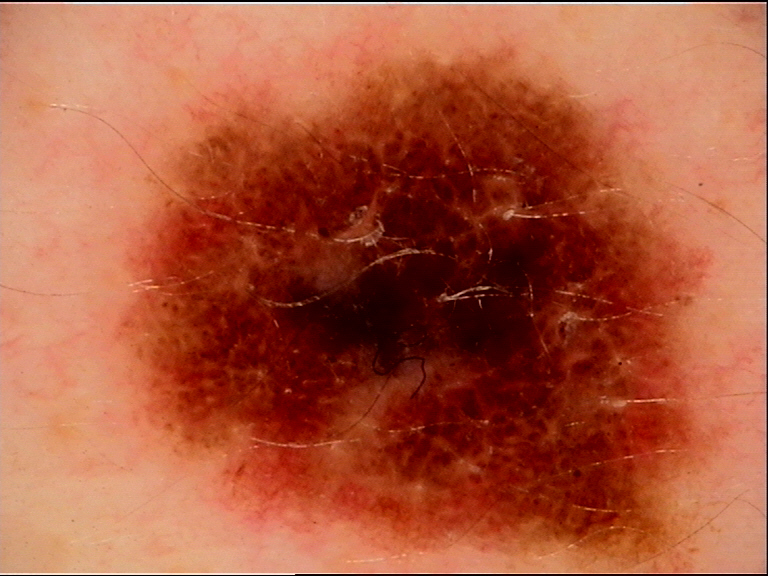Findings: Dermoscopy of a skin lesion. Diagnosis: Confirmed on histopathology as a malignancy — a melanoma.